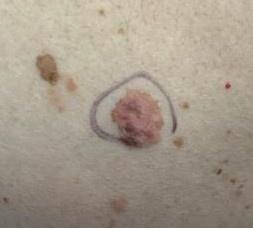A clinical overview photograph of a skin lesion. A male subject in their 60s. The lesion is on the anterior trunk. The biopsy diagnosis was a melanoma.